Dermoscopy of a skin lesion:
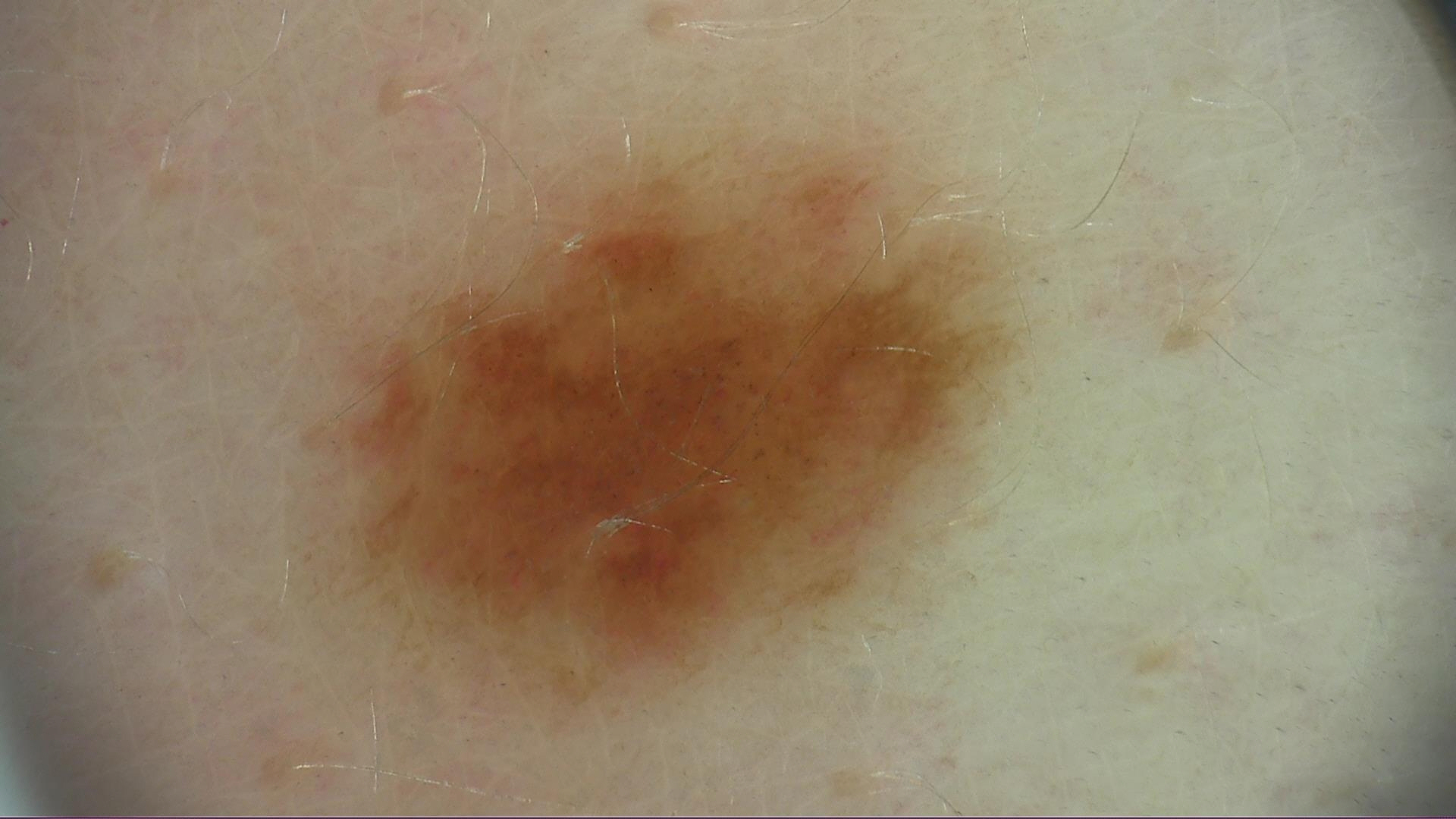Findings:
• assessment: dysplastic junctional nevus (expert consensus)